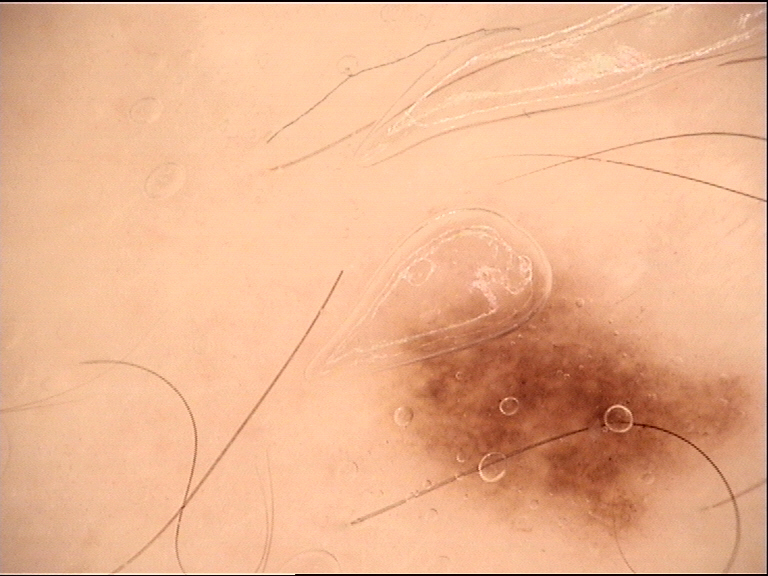Diagnosed as a dysplastic junctional nevus.